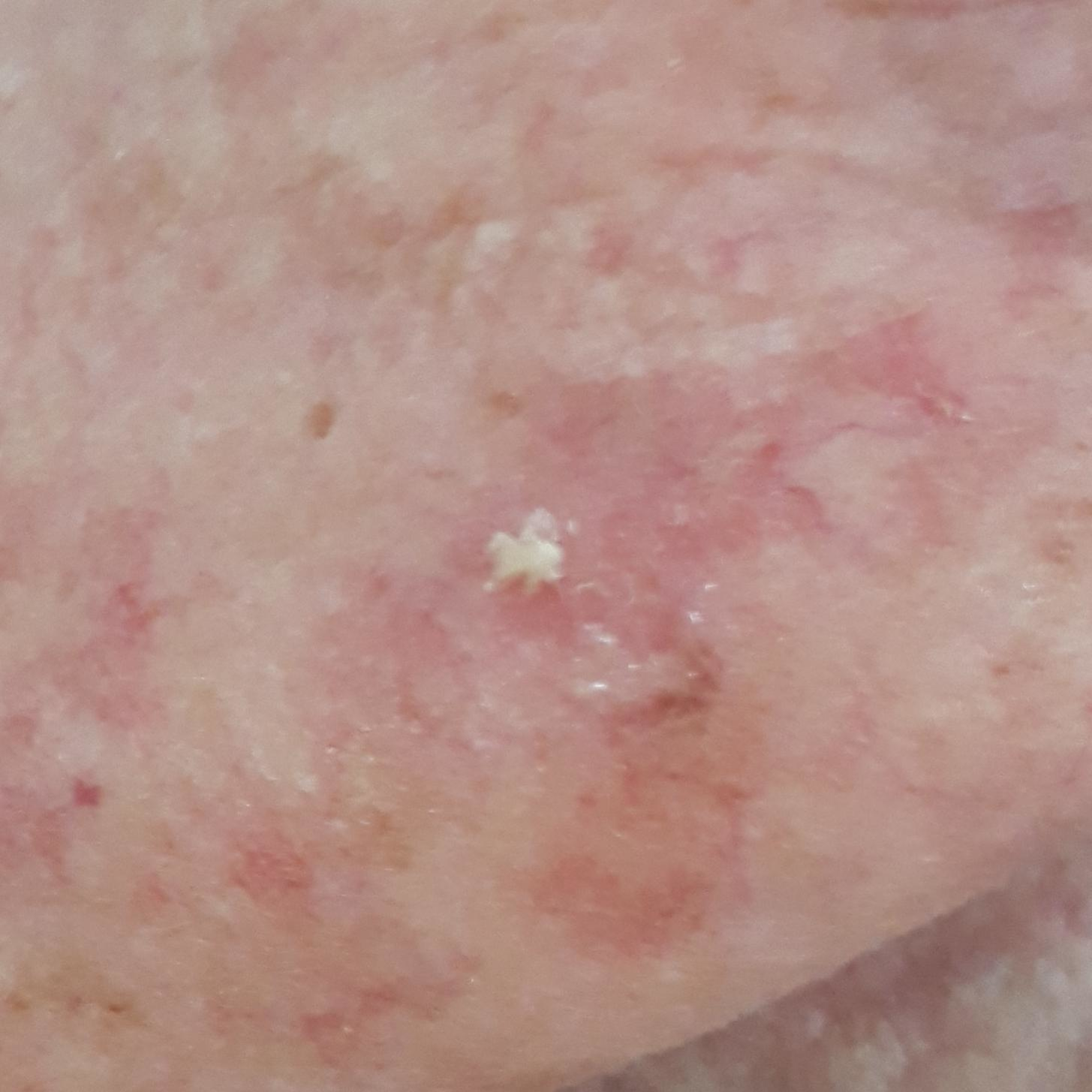A smartphone photograph of a skin lesion. A female subject 90 years old. Located on the face. The patient describes that the lesion has grown and itches. Clinically diagnosed as an actinic keratosis.